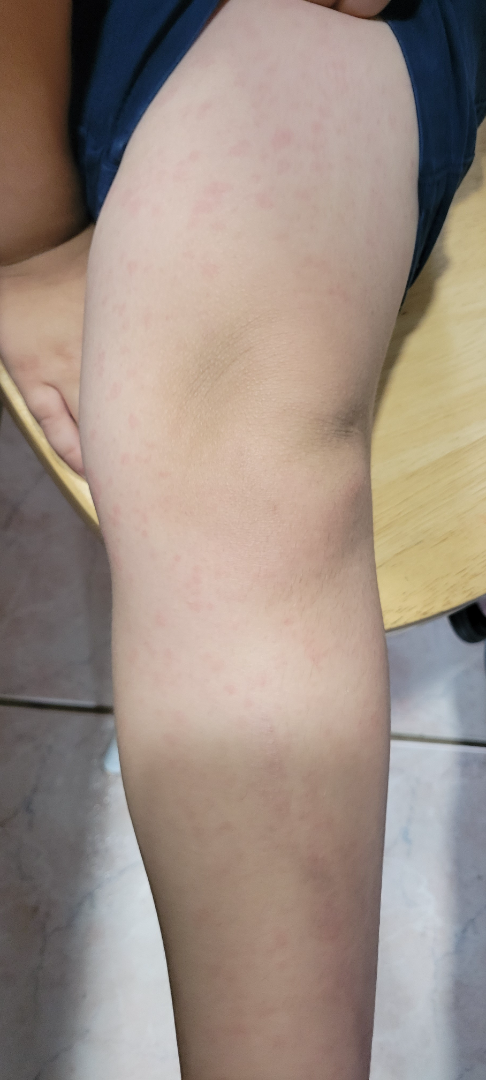assessment = not assessable, systemic symptoms = fever, lesion symptoms = none reported, shot type = close-up, location = leg and arm, skin tone = Fitzpatrick phototype III; lay graders estimated Monk skin tone scale 3 (US pool) or 2 (India pool).